A male subject 70 years old · a smartphone photograph of a skin lesion:
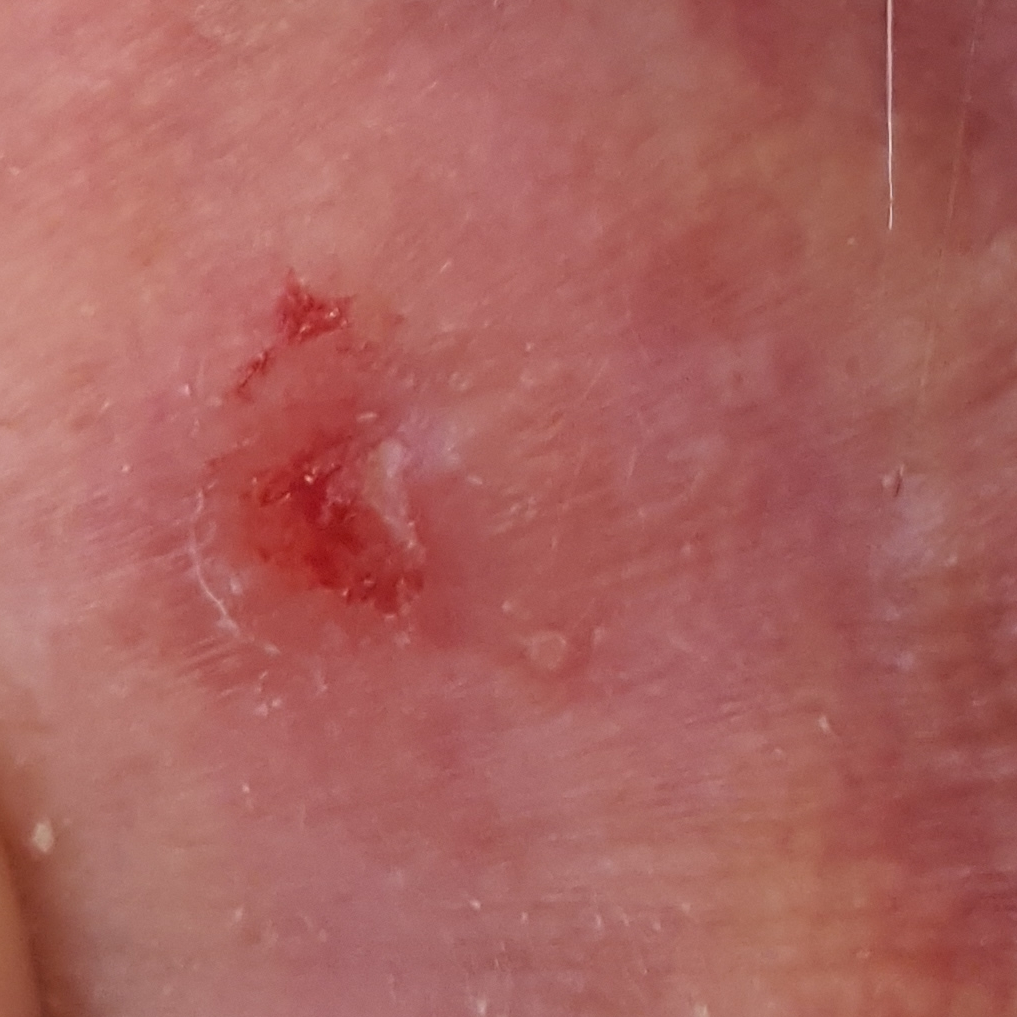Summary:
Located on an ear. By the patient's account, the lesion has grown, is elevated, and has bled, but has not changed and does not itch.
Conclusion:
Confirmed on histopathology as a basal cell carcinoma.